A smartphone photograph of a skin lesion; a male subject in their 80s.
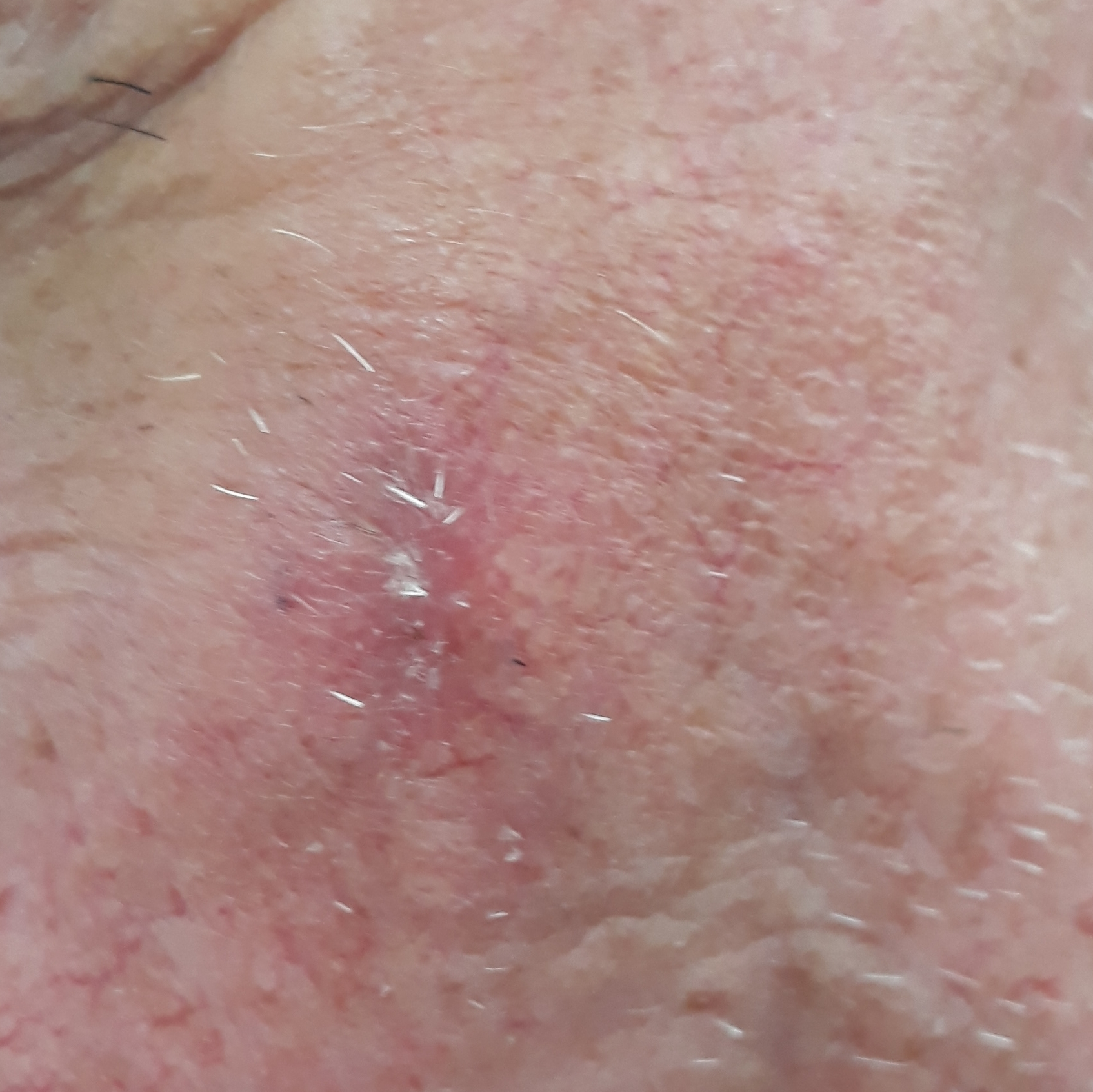| feature | finding |
|---|---|
| site | the face |
| symptoms | elevation, pain, itching, bleeding, growth |
| pathology | basal cell carcinoma (biopsy-proven) |